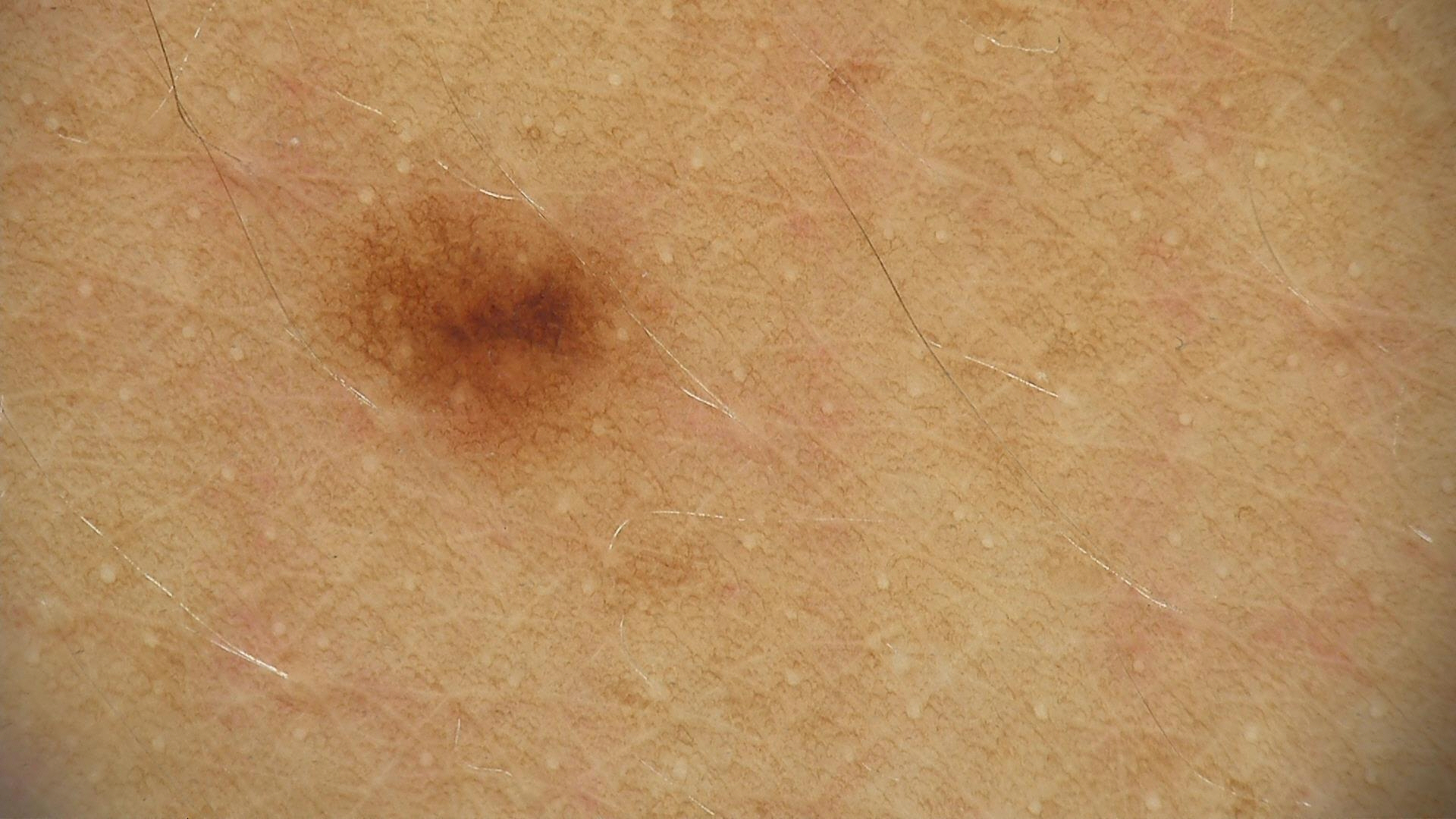Consistent with a dysplastic junctional nevus.